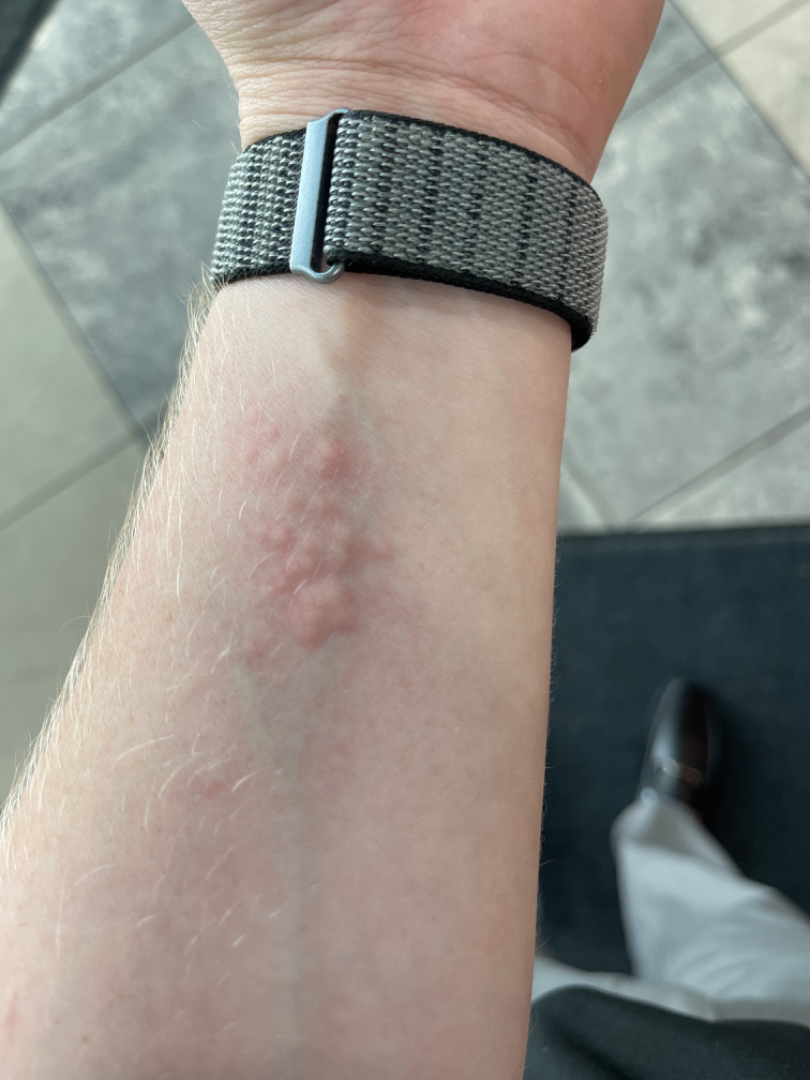The affected area is the arm. The photograph is a close-up of the affected area. The patient reports the lesion is raised or bumpy. Present for about one day. The patient reported no relevant symptoms from the lesion. The patient reported no systemic symptoms. The contributor is a male aged 18–29. One reviewing dermatologist: favoring Allergic Contact Dermatitis; possibly Urticaria.